The lesion involves the front of the torso · the patient reported no systemic symptoms · the patient considered this a rash · the subject is a female aged 30–39 · the photograph was taken at an angle · the patient notes the condition has been present for less than one week · the patient notes the lesion is raised or bumpy · the patient notes itching, bothersome appearance and burning — 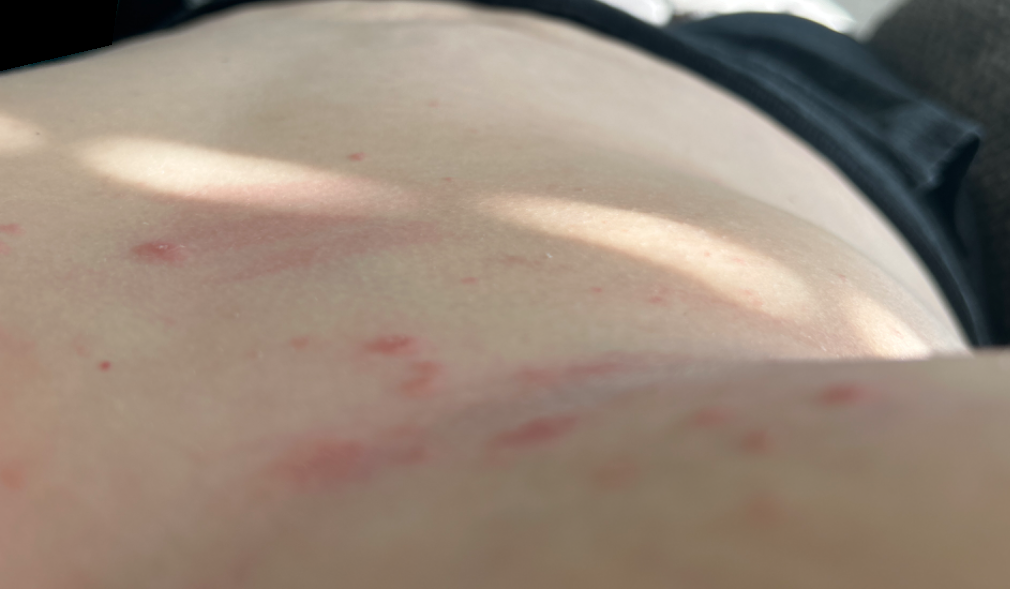Impression: No differential diagnosis could be assigned on photographic review.